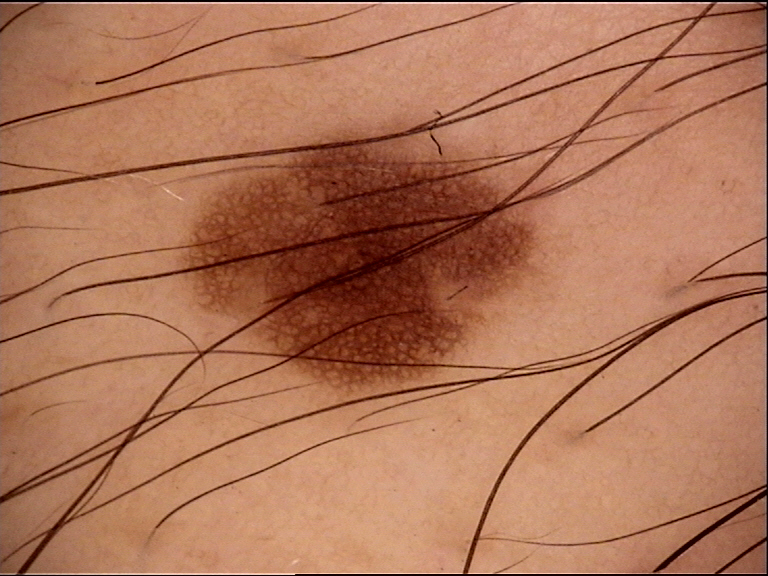image type: dermoscopy | category: banal | assessment: junctional nevus (expert consensus).